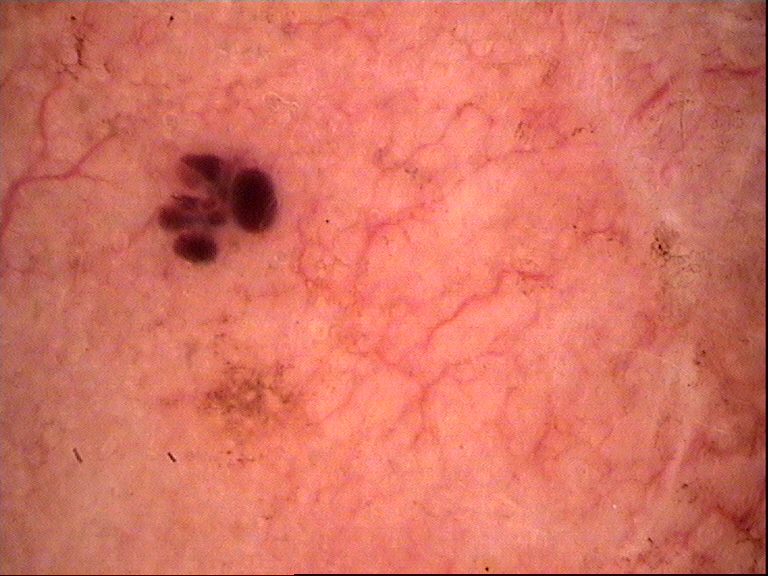modality: dermoscopy
class: basal cell carcinoma (biopsy-proven)